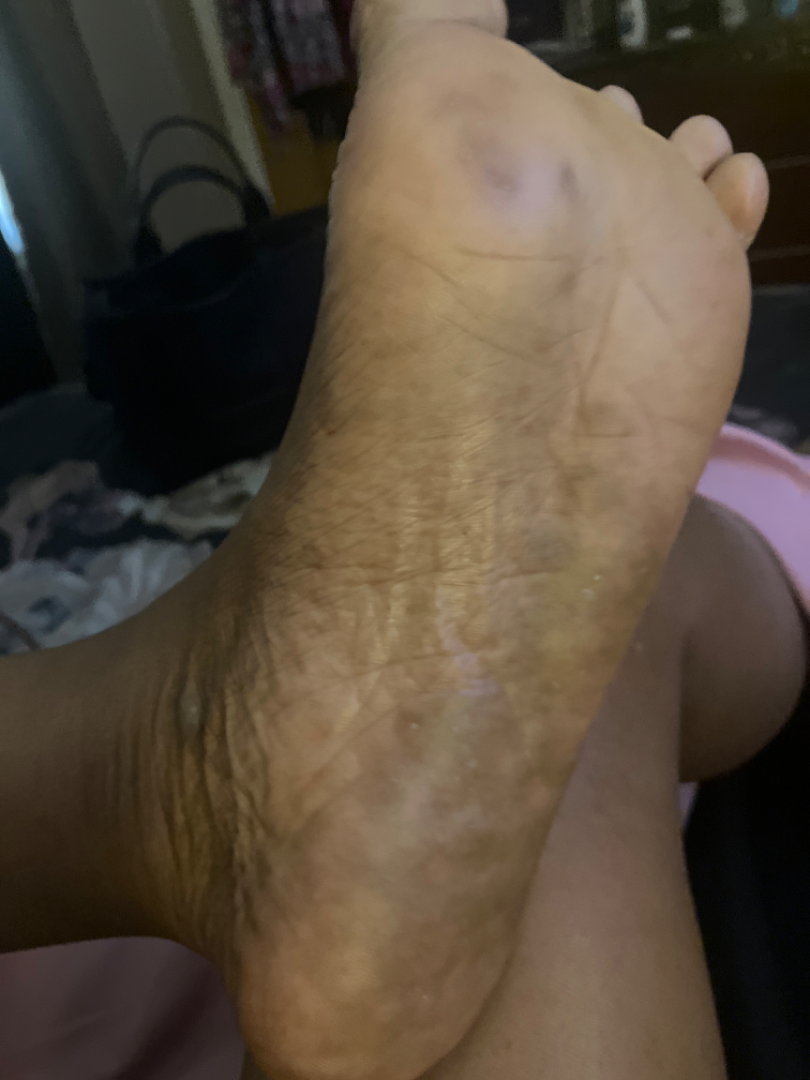Symptoms reported: darkening, itching and pain. The lesion involves the sole of the foot and top or side of the foot. The patient indicates the condition has been present for one to four weeks. The contributor is a female aged 40–49. The photograph was taken at an angle. Fitzpatrick skin type V. The patient indicates the lesion is raised or bumpy and rough or flaky. The reviewing panel's impression was: Psoriasis (favored); Keratoderma (possible); Tinea (unlikely); Eczema (unlikely).